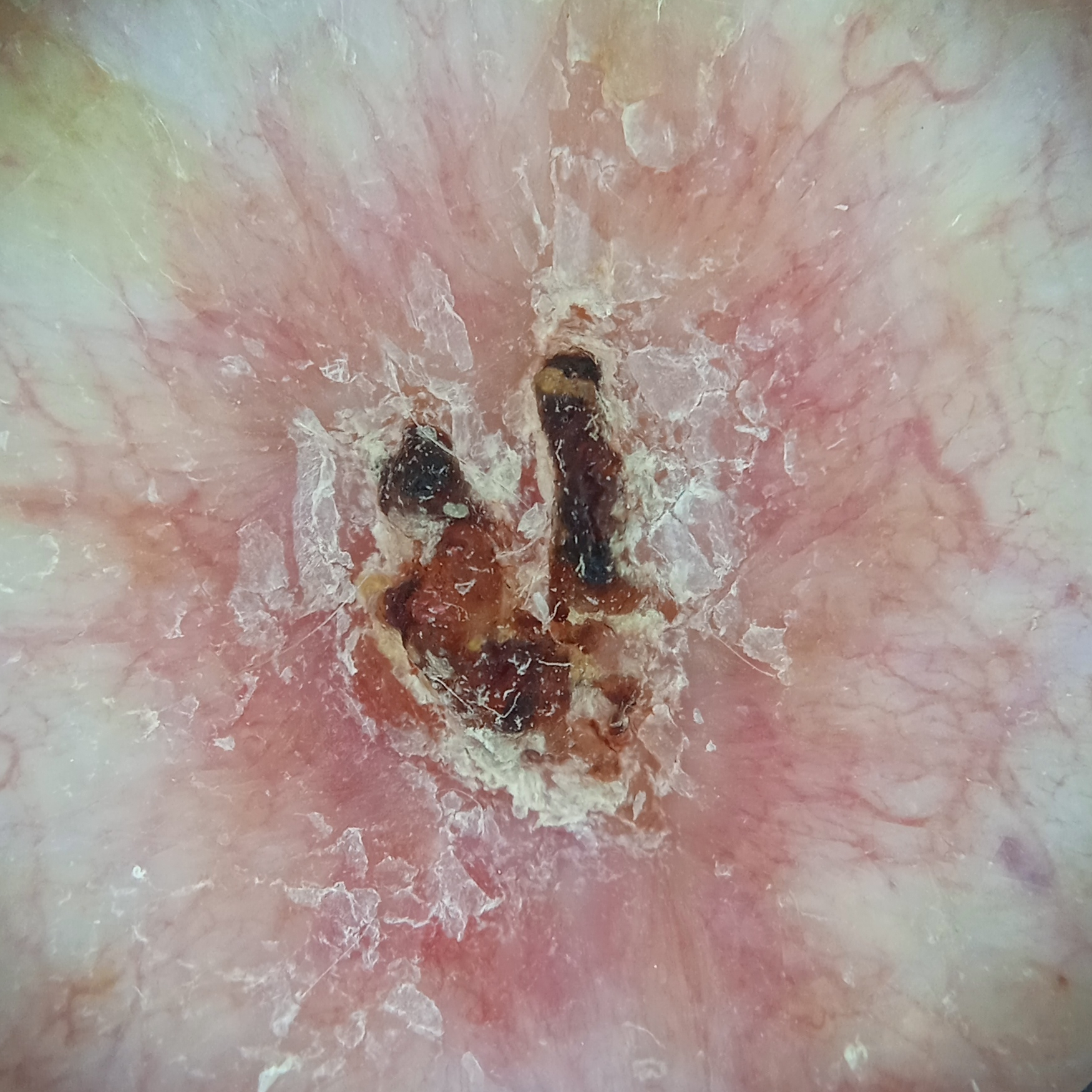image: dermoscopic image
diagnosis:
  name: basal cell carcinoma
  malignancy: malignant
  unanimous: false
  certainty: good